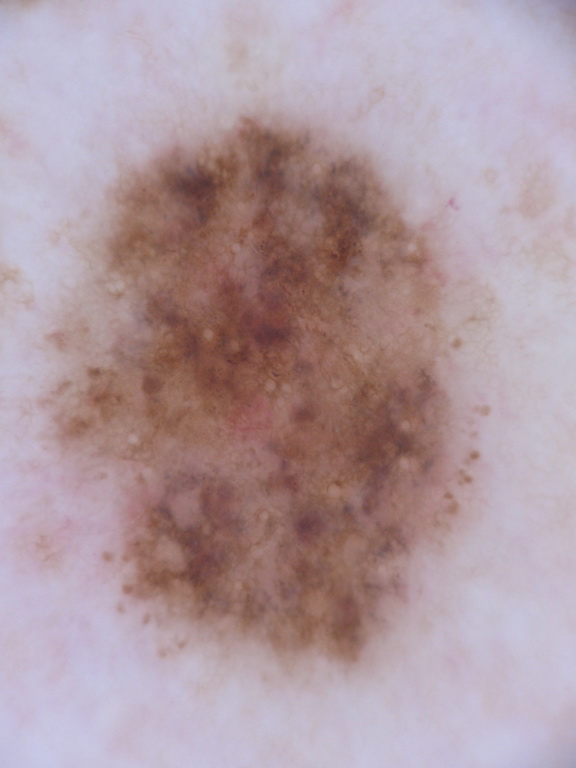Case summary:
A dermoscopic view of a skin lesion. As (left, top, right, bottom), the lesion is bounded by <box>34, 97, 491, 685</box>.
Conclusion:
The clinical diagnosis was a melanocytic nevus, a benign skin lesion.